The affected area is the front of the torso, arm, leg and back of the hand · a close-up photograph:
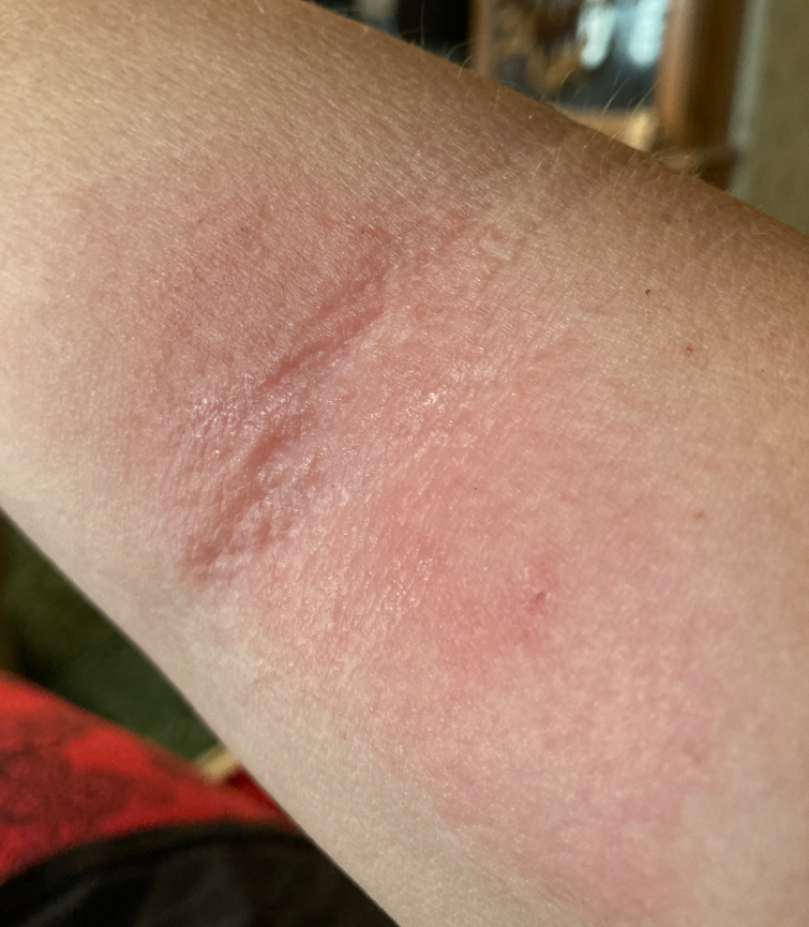<case>
<differential>
  <leading>Eczema</leading>
  <considered>Tinea, Psoriasis</considered>
</differential>
</case>